A dermoscopic photograph of a skin lesion.
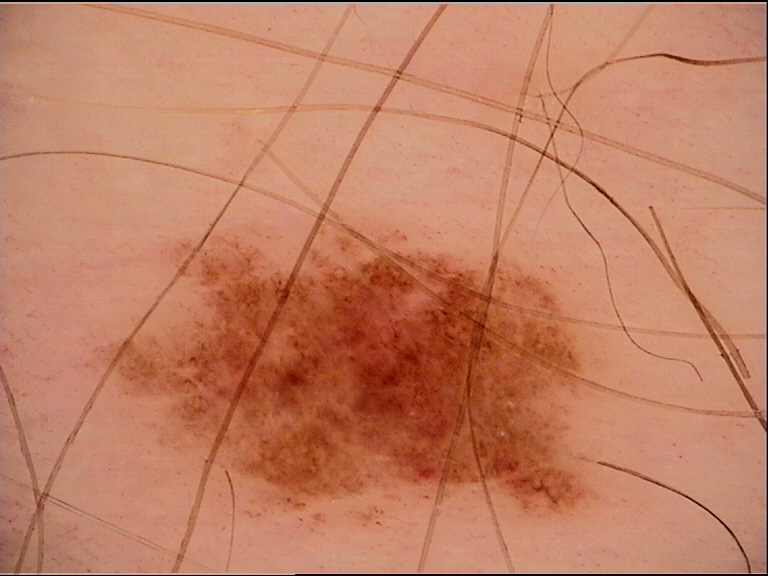Findings:
• diagnostic label: dysplastic junctional nevus (expert consensus)